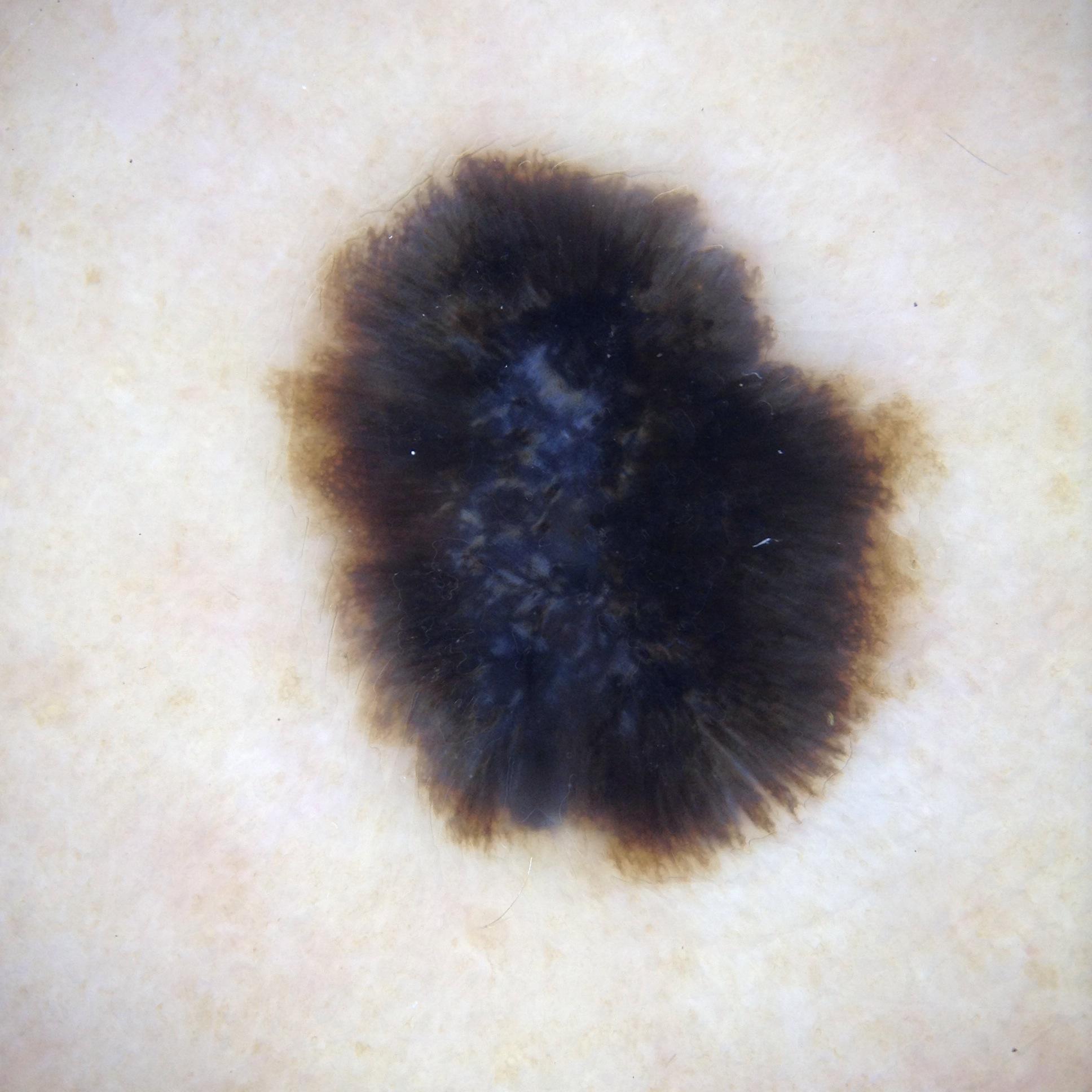A female patient approximately 50 years of age. A dermoscopic view of a skin lesion. With coordinates (x1, y1, x2, y2), the lesion is located at 275 142 935 885. Dermoscopic review identifies pigment network and streaks, with no milia-like cysts, globules, or negative network. A moderately sized lesion. Confirmed on histopathology as a melanoma.